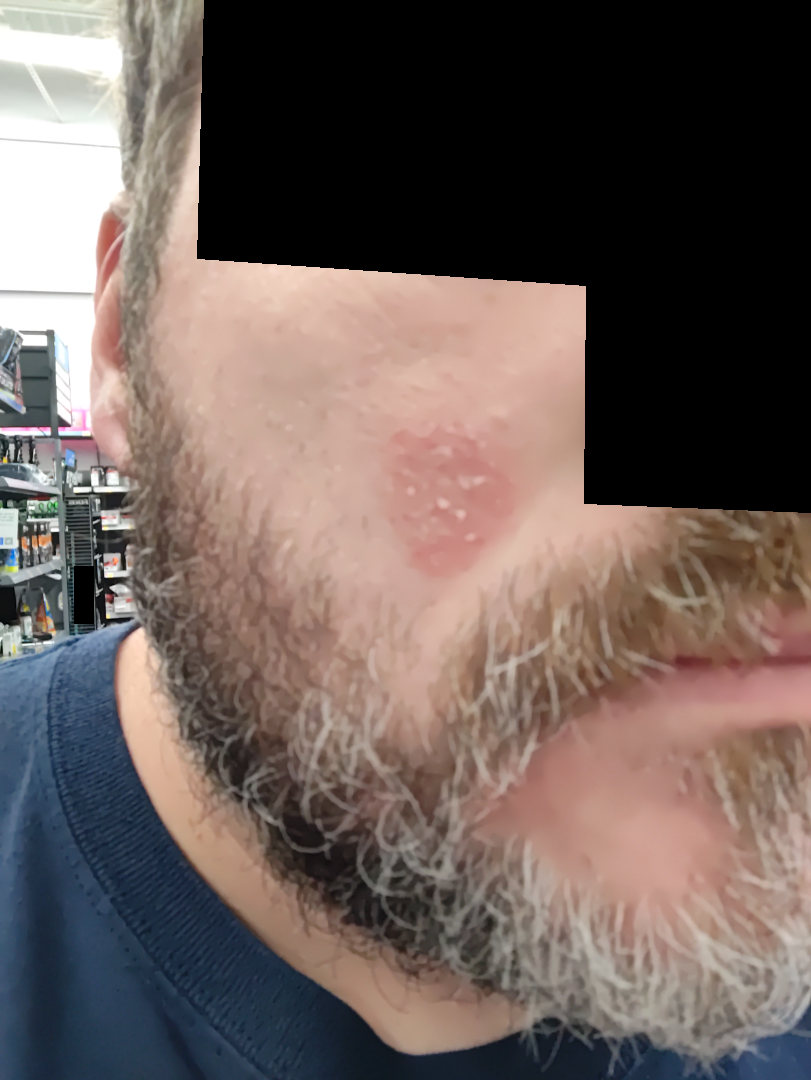The photograph is a close-up of the affected area. Seborrheic Dermatitis (leading); Tinea (possible); Eczema (possible).